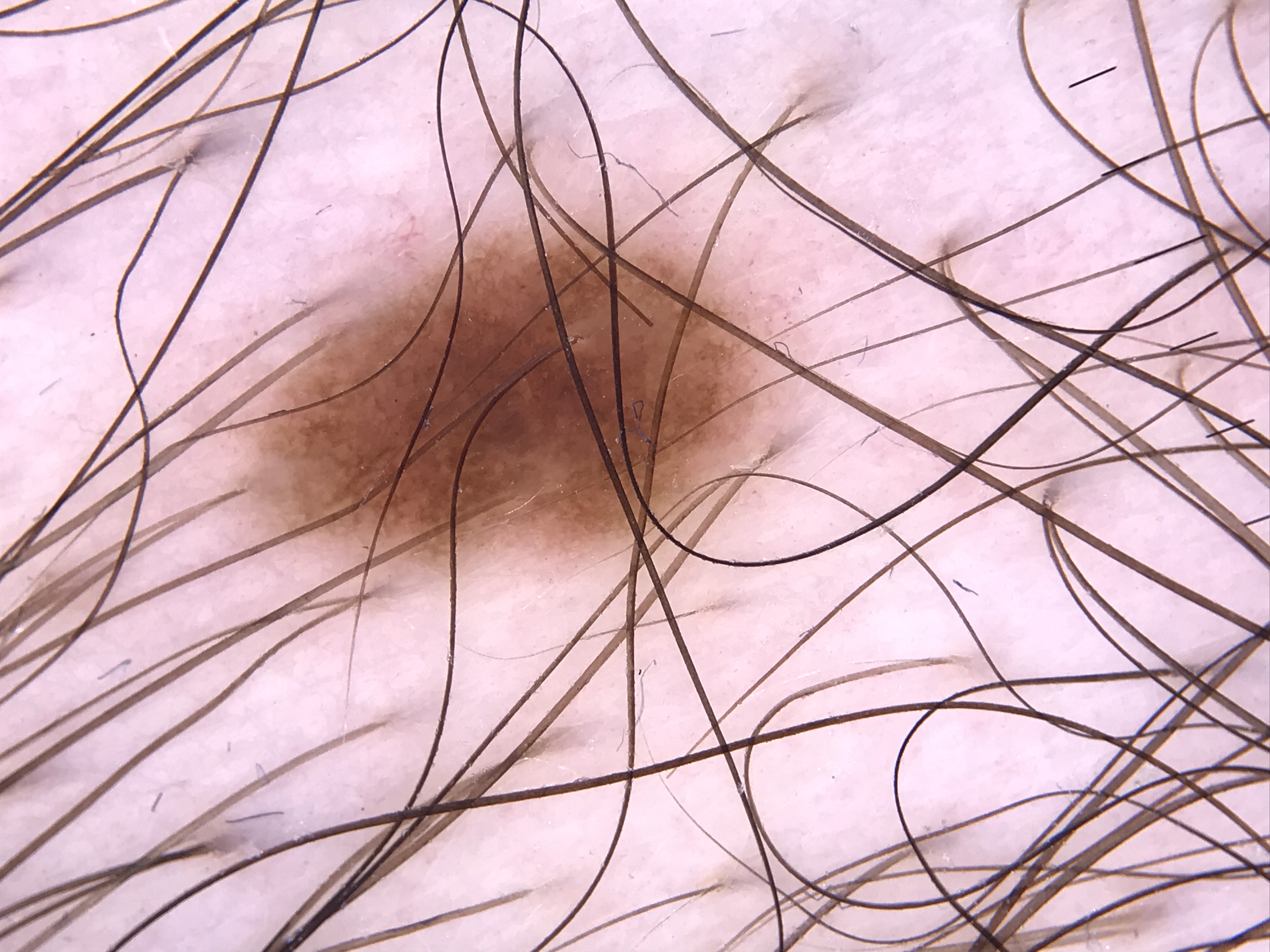Q: What is this lesion?
A: dysplastic junctional nevus (expert consensus)